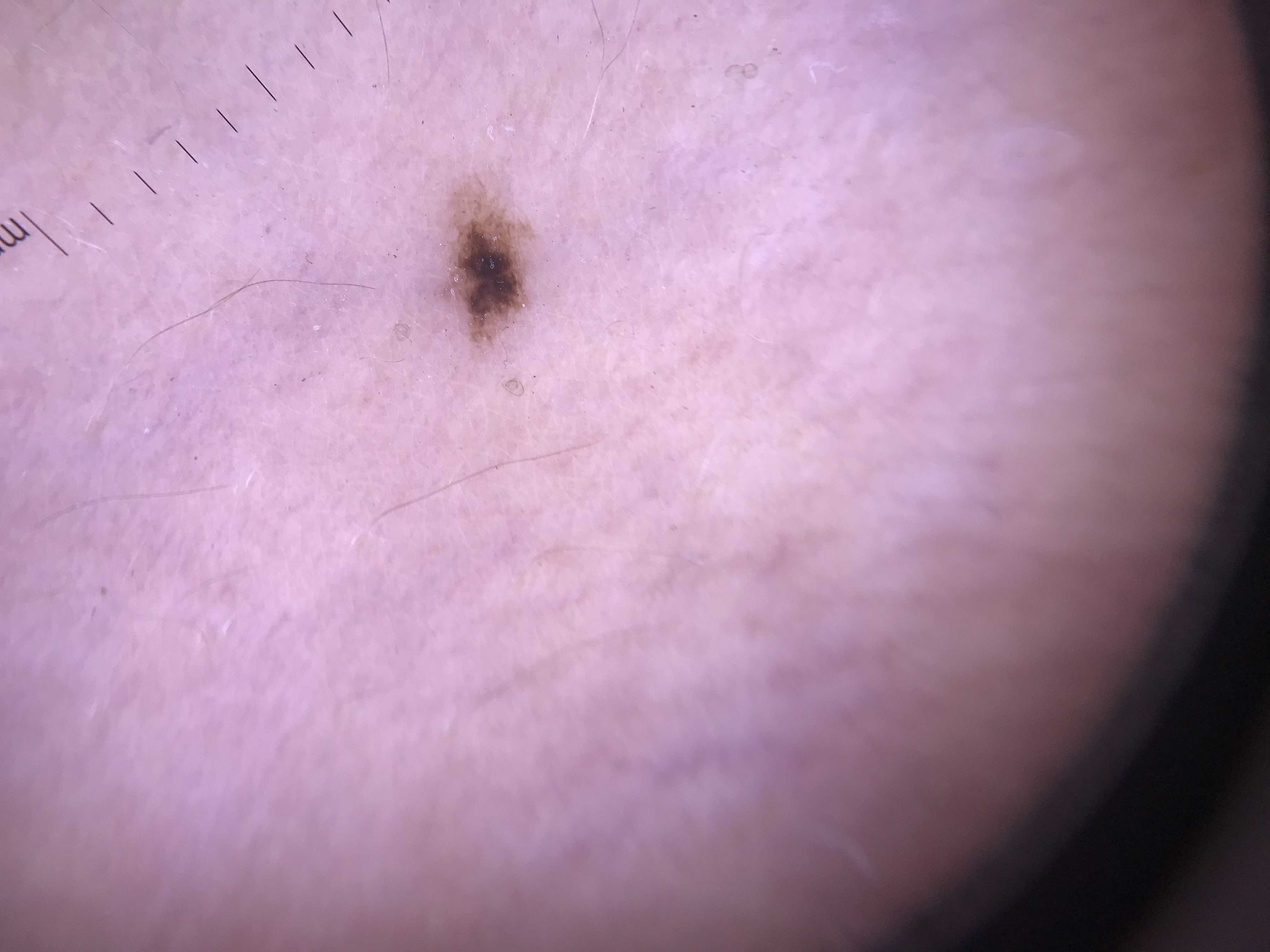Case: A dermoscopic close-up of a skin lesion. Conclusion: The diagnostic label was a benign lesion — a dysplastic junctional nevus.